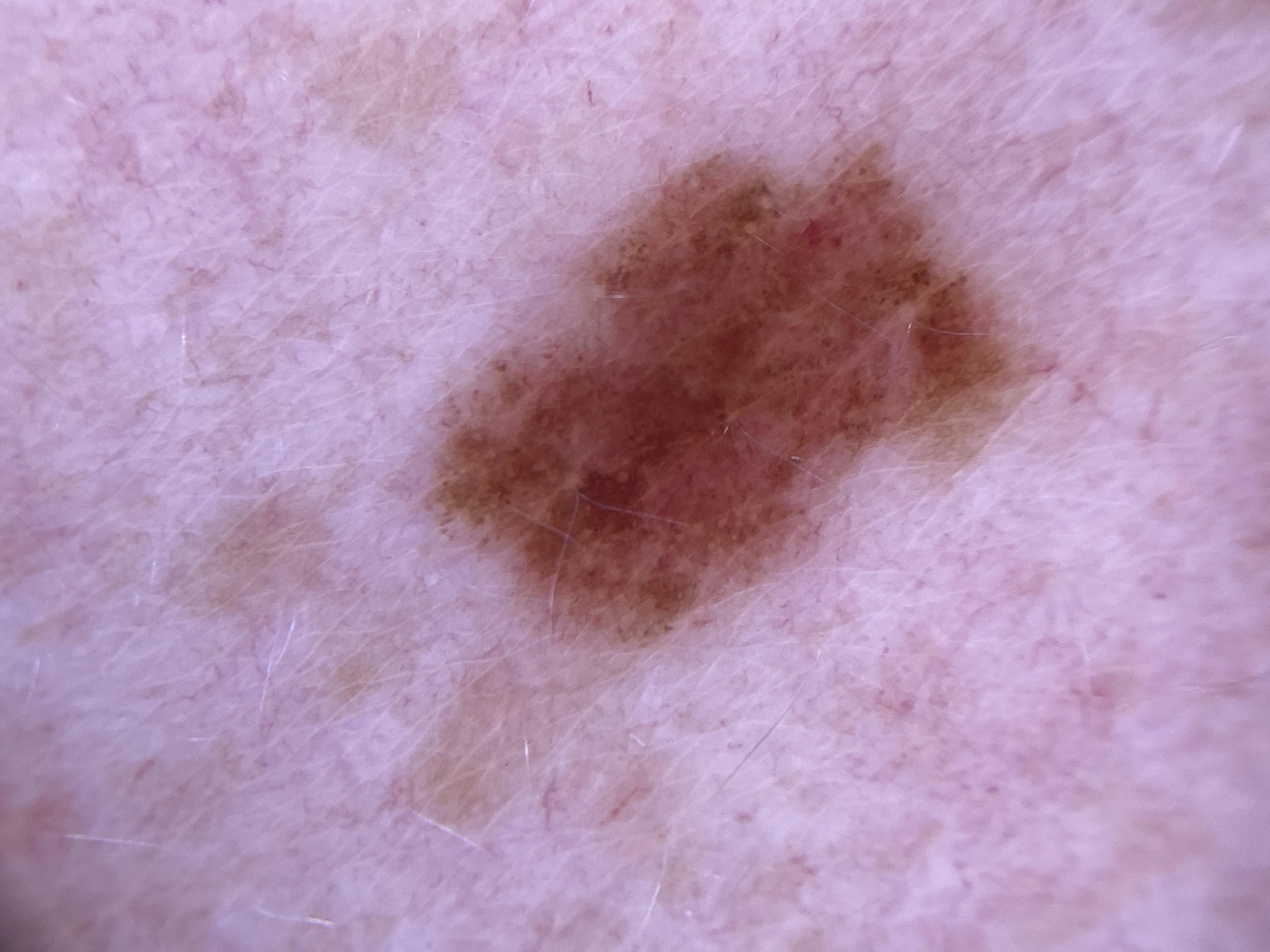Findings:
Dermoscopy of a skin lesion. The chart documents a prior melanoma. A male subject aged approximately 45. The lesion is located on the trunk.
Assessment:
Consistent with a nevus.